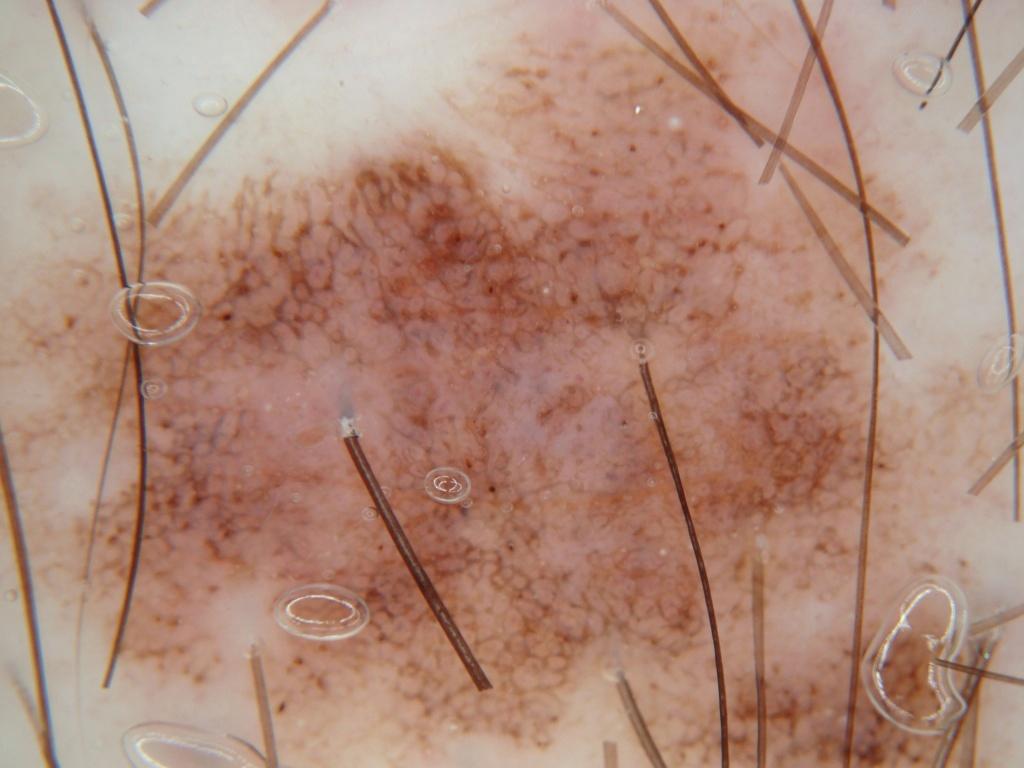{"image": {"modality": "dermoscopy"}, "lesion_location": "spans the dermoscopic field", "dermoscopic_features": {"present": ["milia-like cysts", "pigment network"], "absent": ["negative network", "streaks"]}, "diagnosis": {"name": "melanocytic nevus", "malignancy": "benign", "lineage": "melanocytic", "provenance": "clinical"}}